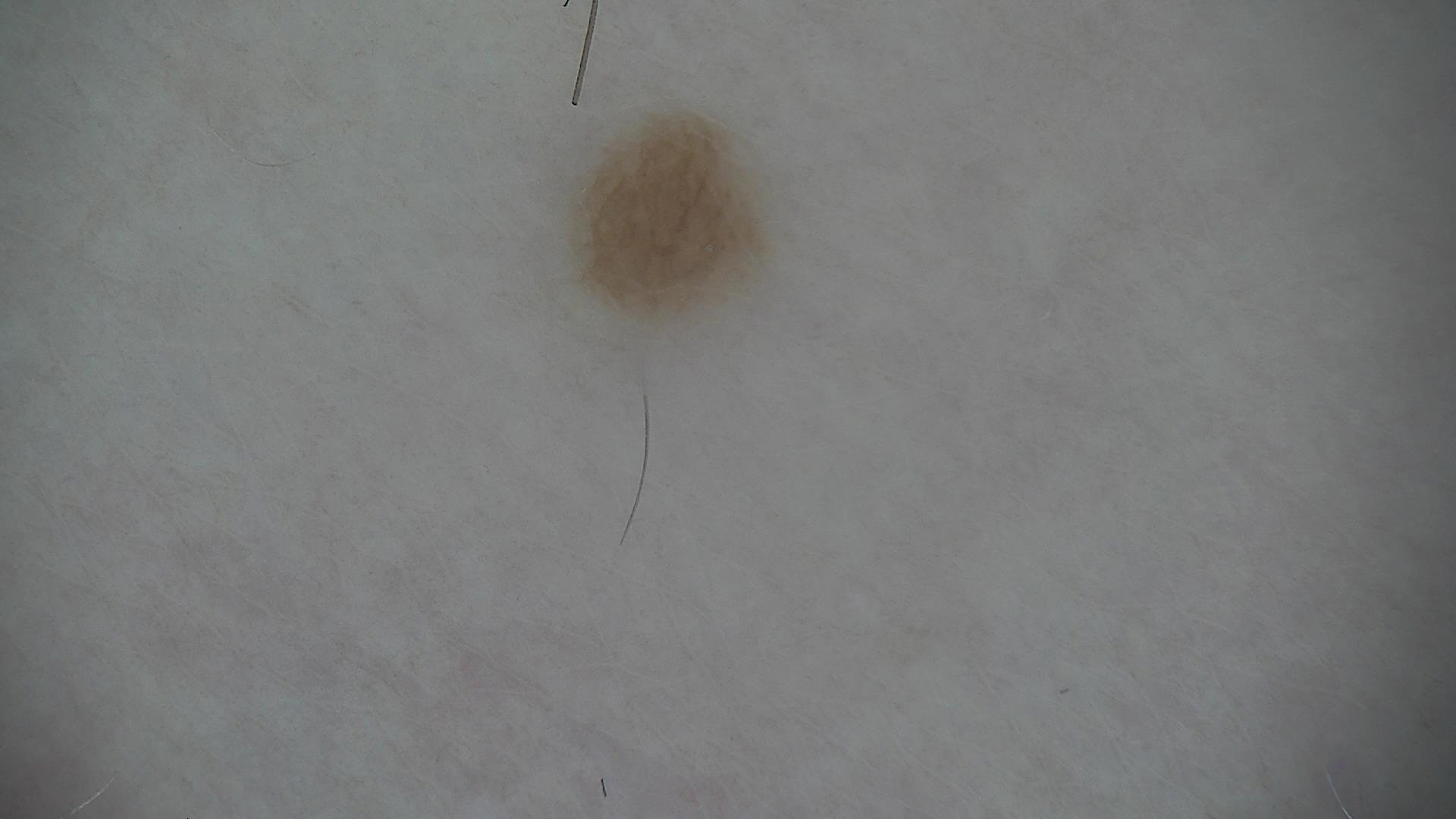Case:
• image type: dermatoscopy
• diagnostic label: dysplastic junctional nevus (expert consensus)